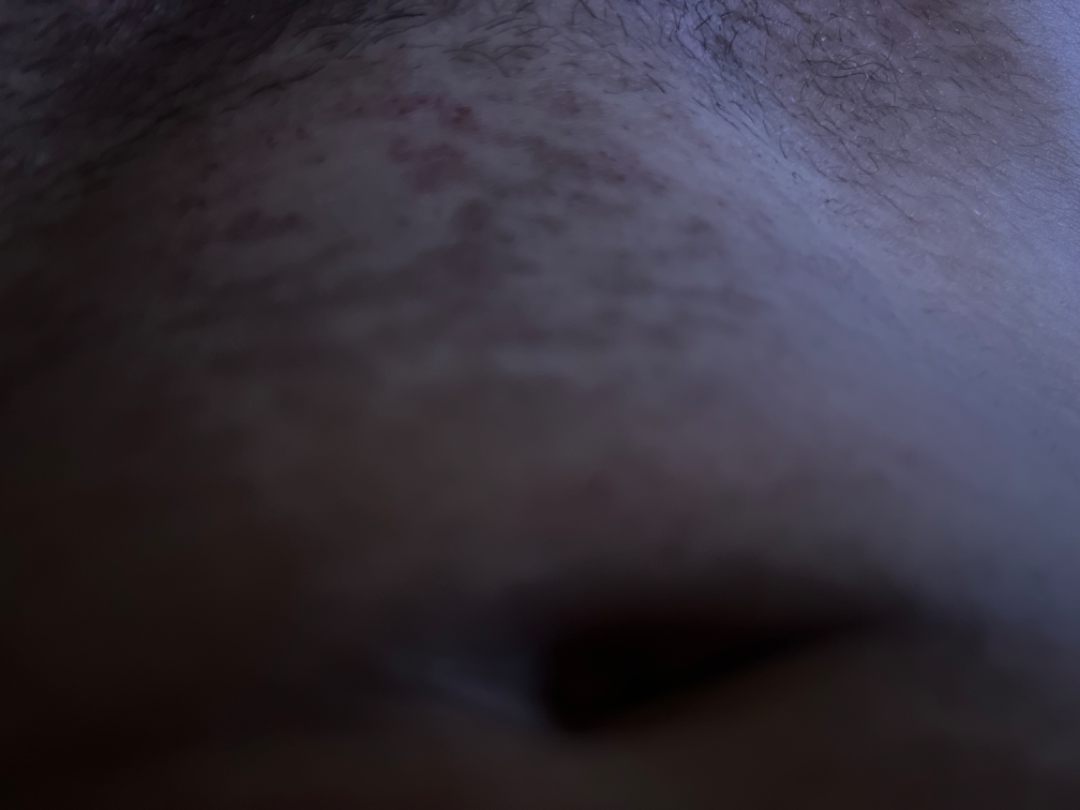The contributor is male.
An image taken at an angle.
On dermatologist assessment of the image, most consistent with Confluent and reticulate papillomatosis; an alternative is Tinea Versicolor; with consideration of Post-Inflammatory hyperpigmentation.